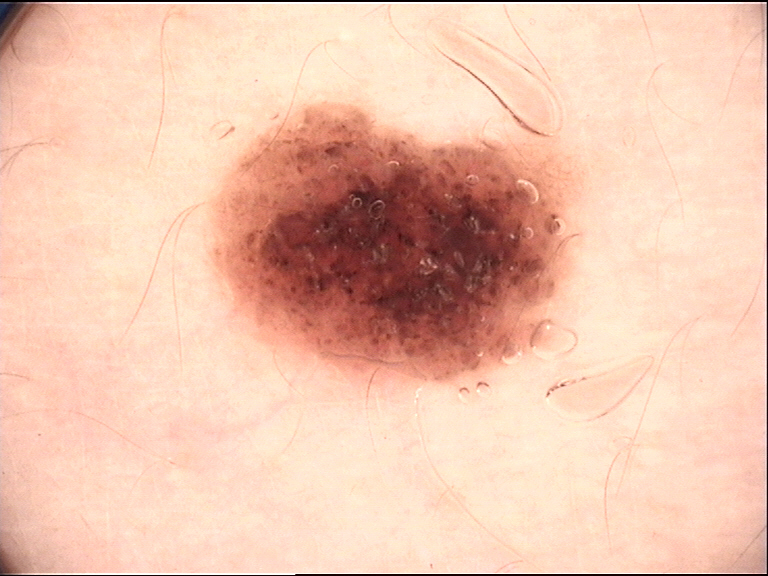Findings:
• assessment — dysplastic compound nevus (expert consensus)